The contributor is 40–49, female. The lesion involves the head or neck. The photograph was taken at an angle — 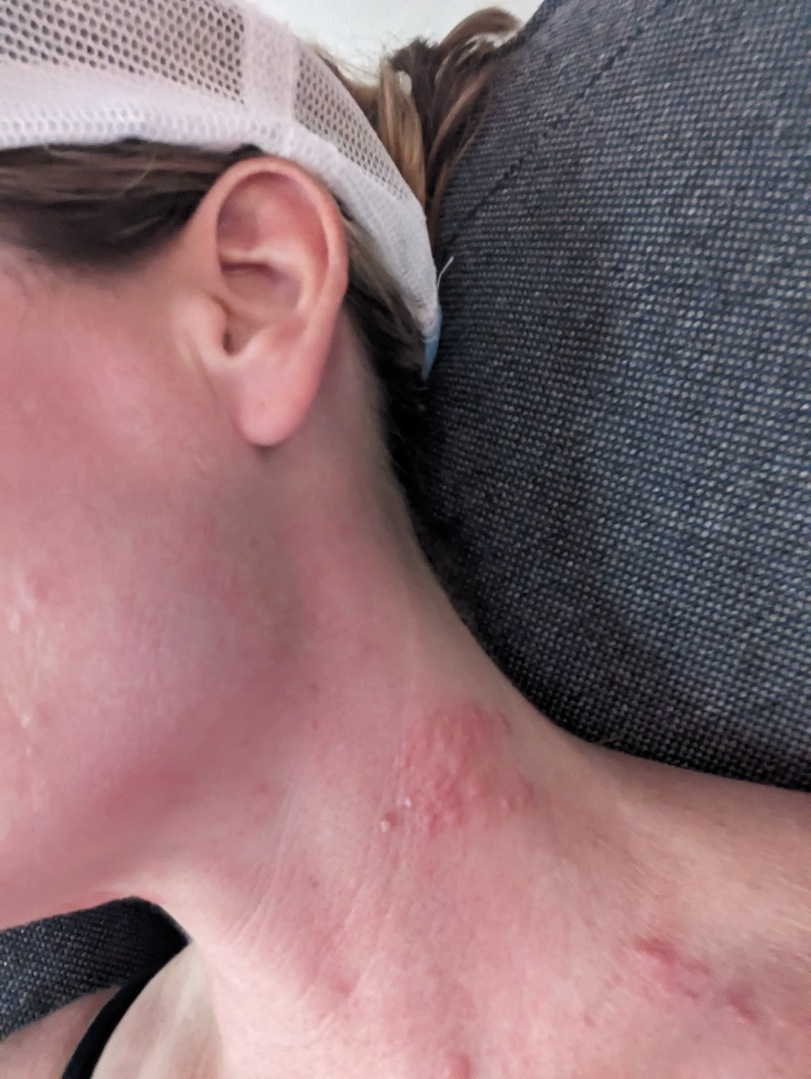Notes:
- skin tone · Fitzpatrick phototype II
- symptoms · itching
- present for · less than one week
- diagnostic considerations · Herpes Zoster (67%); Contact dermatitis (33%)